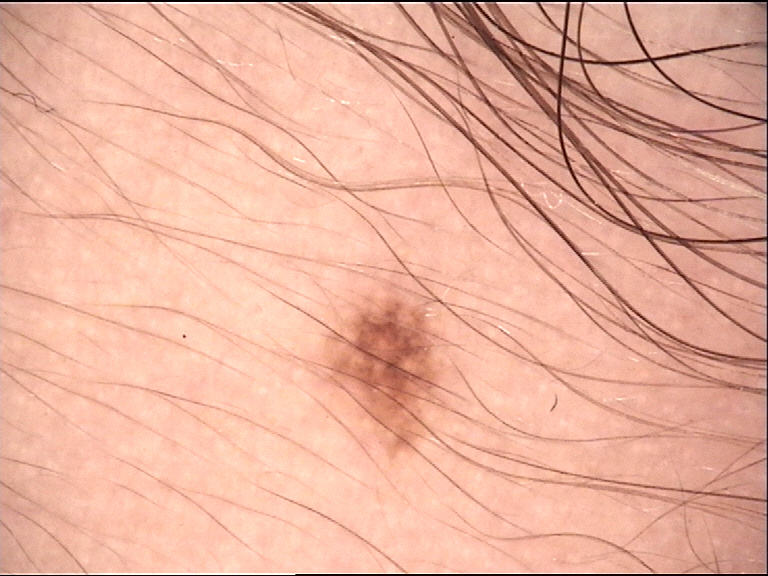A skin lesion imaged with a dermatoscope. The architecture is that of a compound, banal lesion. Classified as a Miescher nevus.